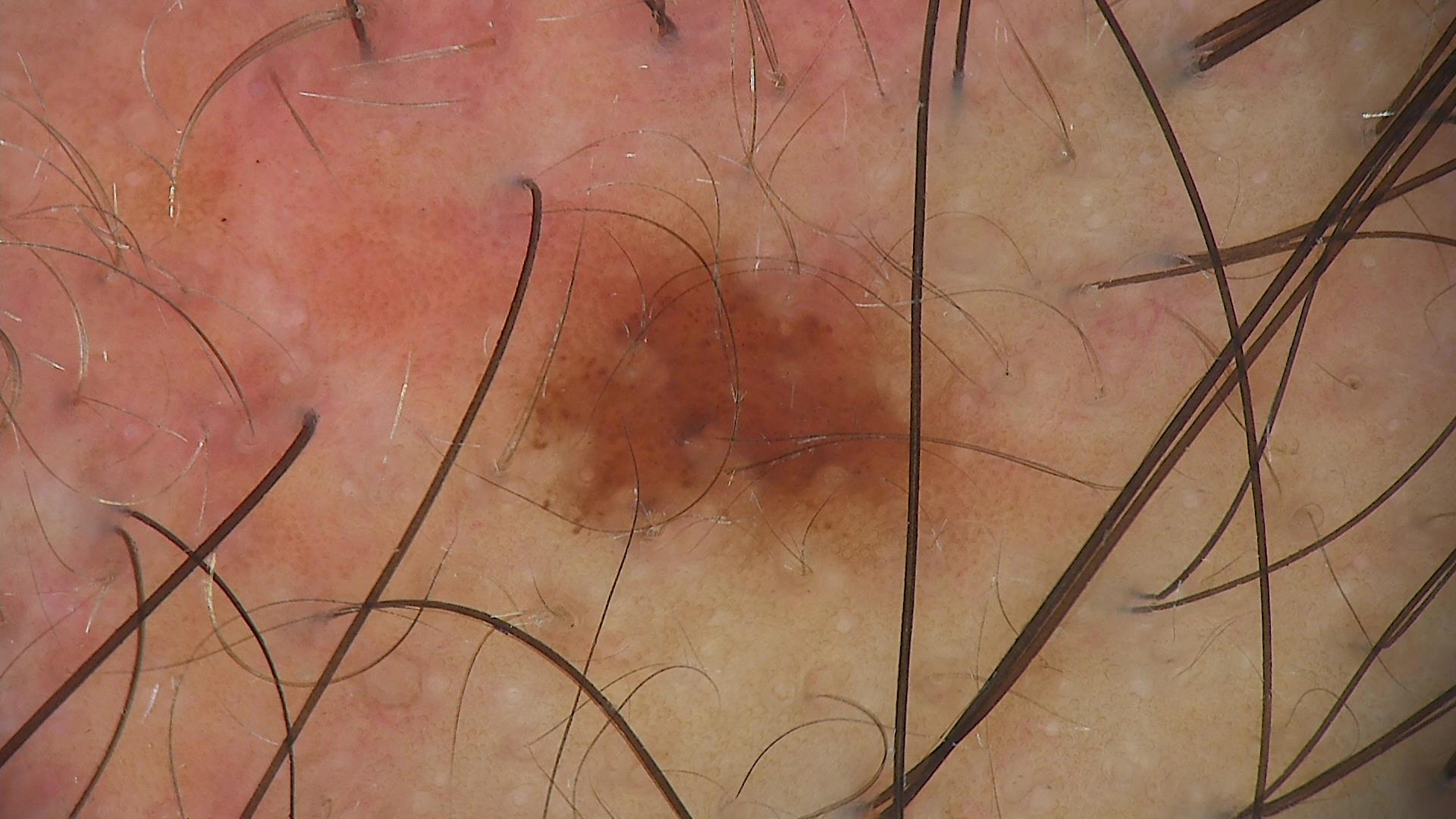Impression:
Labeled as a dysplastic junctional nevus.